This image was taken at an angle. The arm is involved: 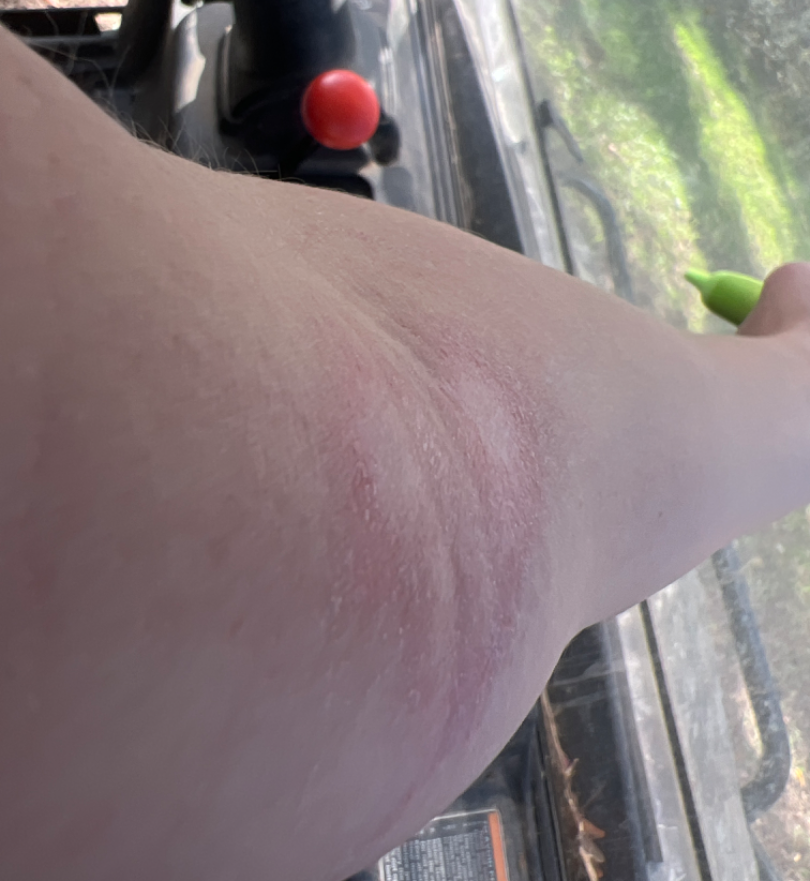Q: What conditions are considered?
A: most consistent with Morphea/Scleroderma; also on the differential is Eczema